This image was taken at an angle · female contributor, age 30–39 · the affected area is the head or neck · self-categorized by the patient as a rash · associated systemic symptoms include fatigue · the patient reports the condition has been present for less than one week — 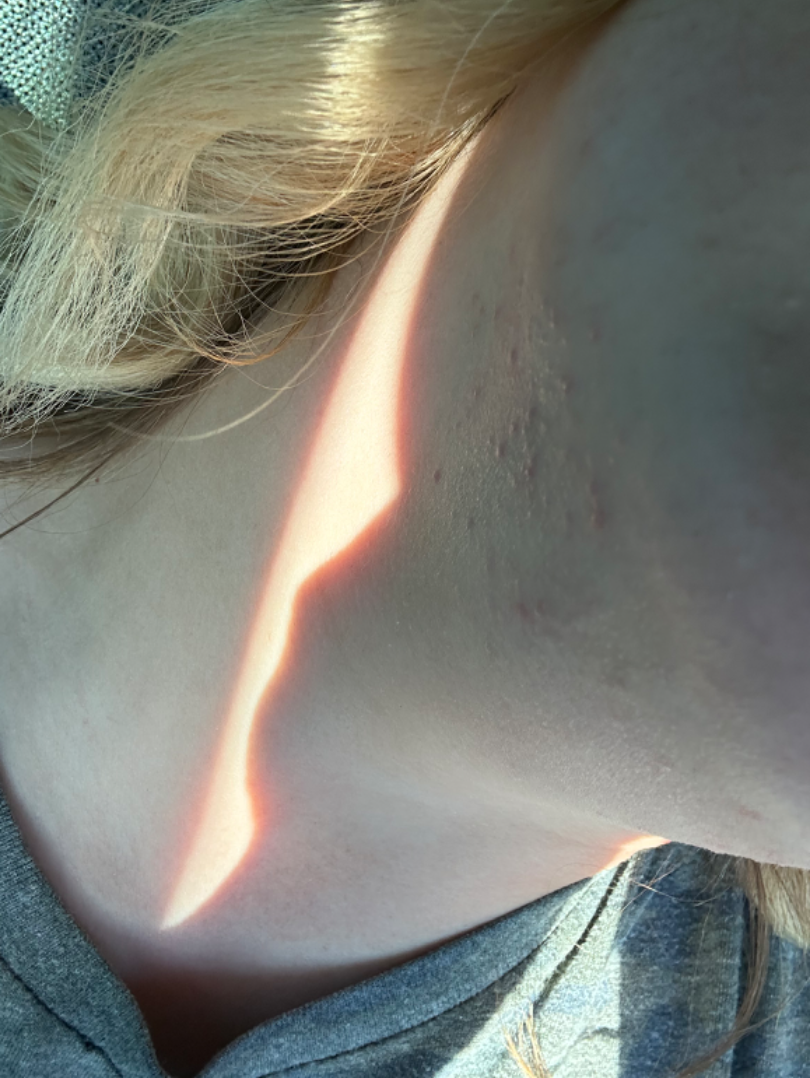differential diagnosis = the impression is Acne.